Close-up view:
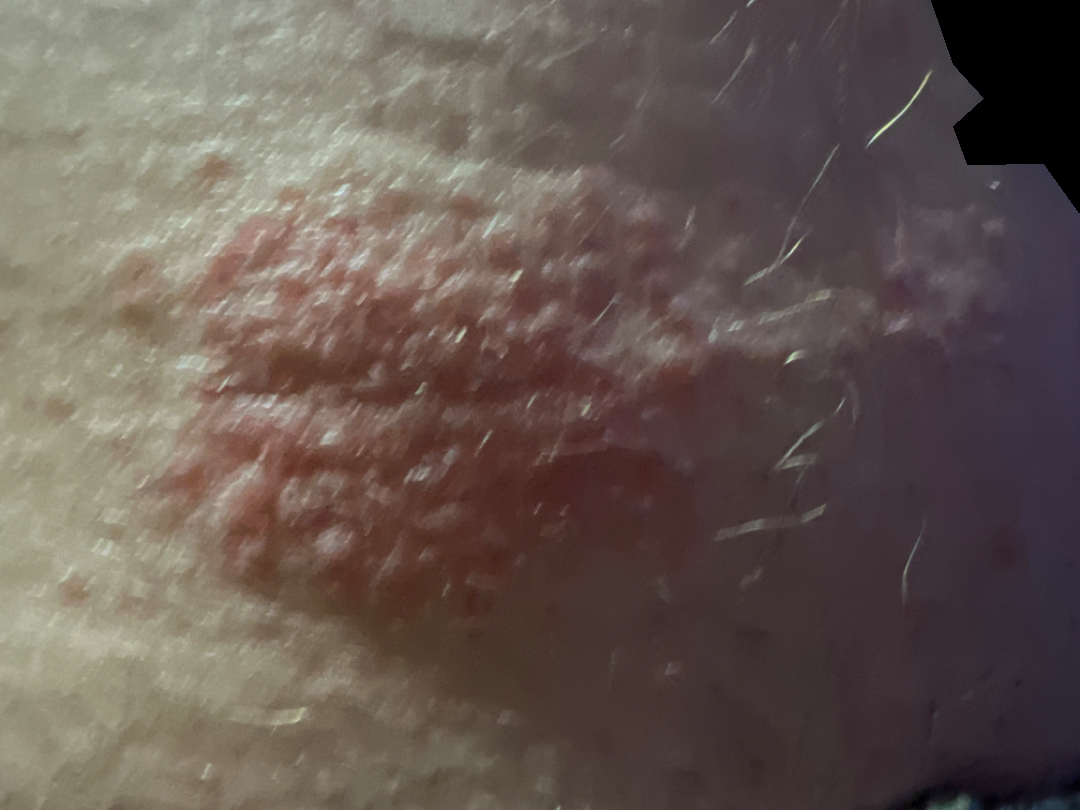Diagnostic features were not clearly distinguishable in this photograph.